Located on the leg; the contributor is 40–49, female; this is a close-up image:
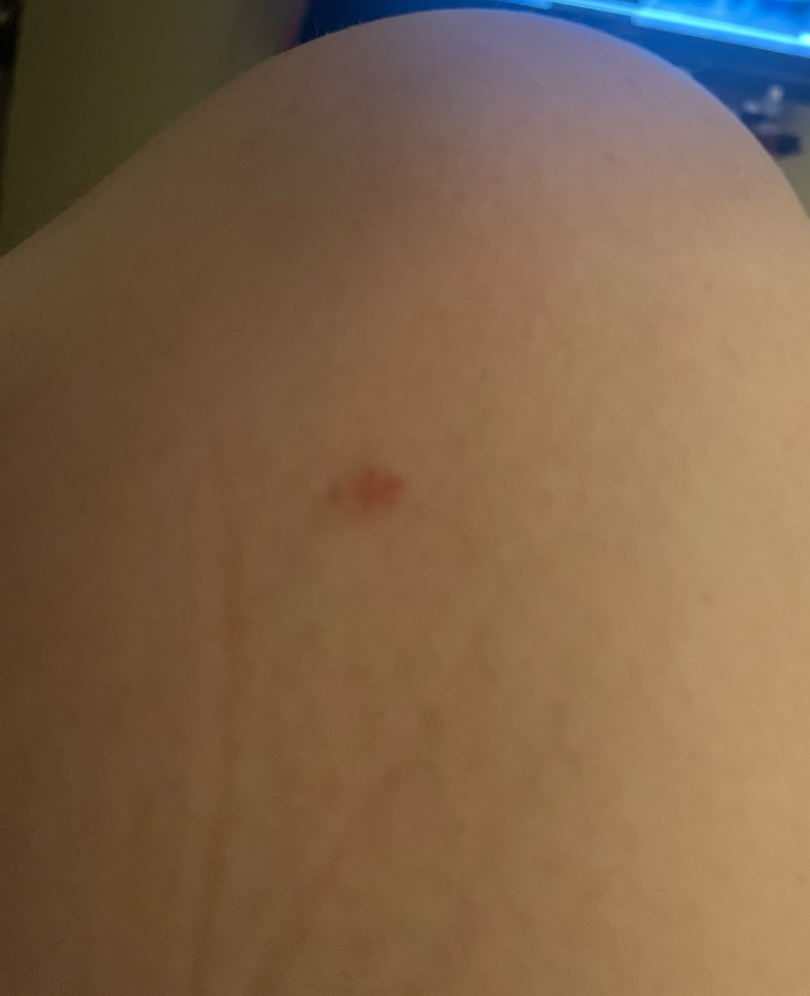Findings:
- assessment — could not be assessed
- symptoms — itching
- systemic symptoms — none reported
- skin tone — self-reported Fitzpatrick phototype II; lay graders estimated a MST of 3
- texture — raised or bumpy
- present for — less than one week